A skin lesion imaged with a dermatoscope; a female patient, in their mid-50s: 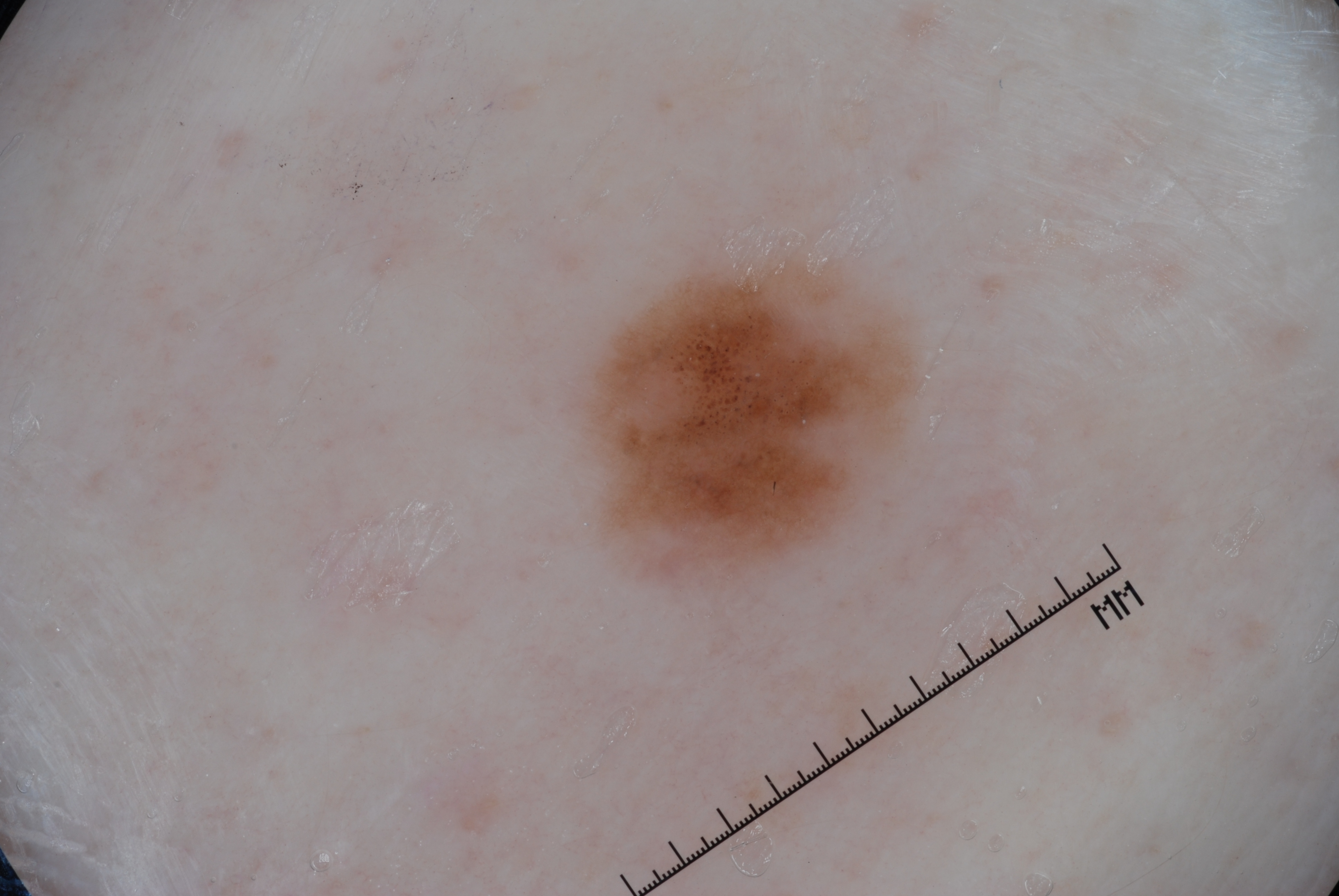dermoscopic findings — milia-like cysts and pigment network; absent: streaks and negative network | size — ~7% of the field | lesion bbox — (586, 259, 910, 588) | impression — a melanocytic nevus.